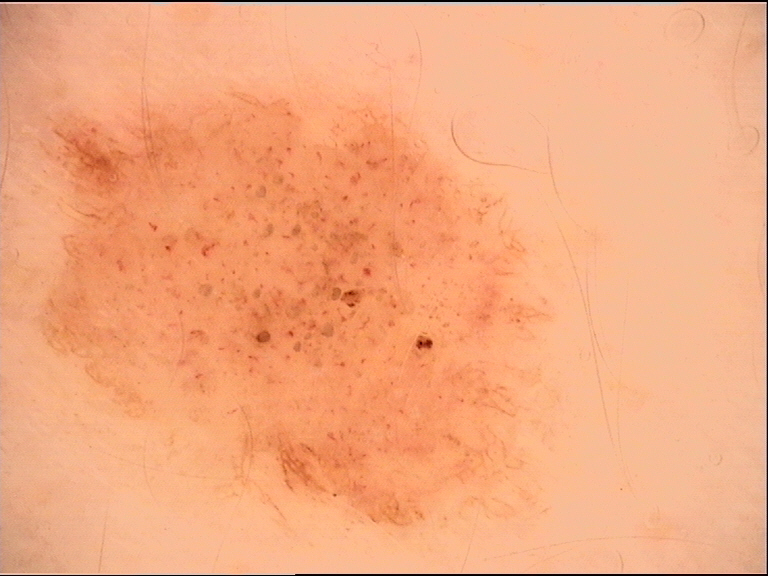A dermatoscopic image of a skin lesion.
The diagnosis was a dysplastic junctional nevus.